Dermoscopy of a skin lesion: 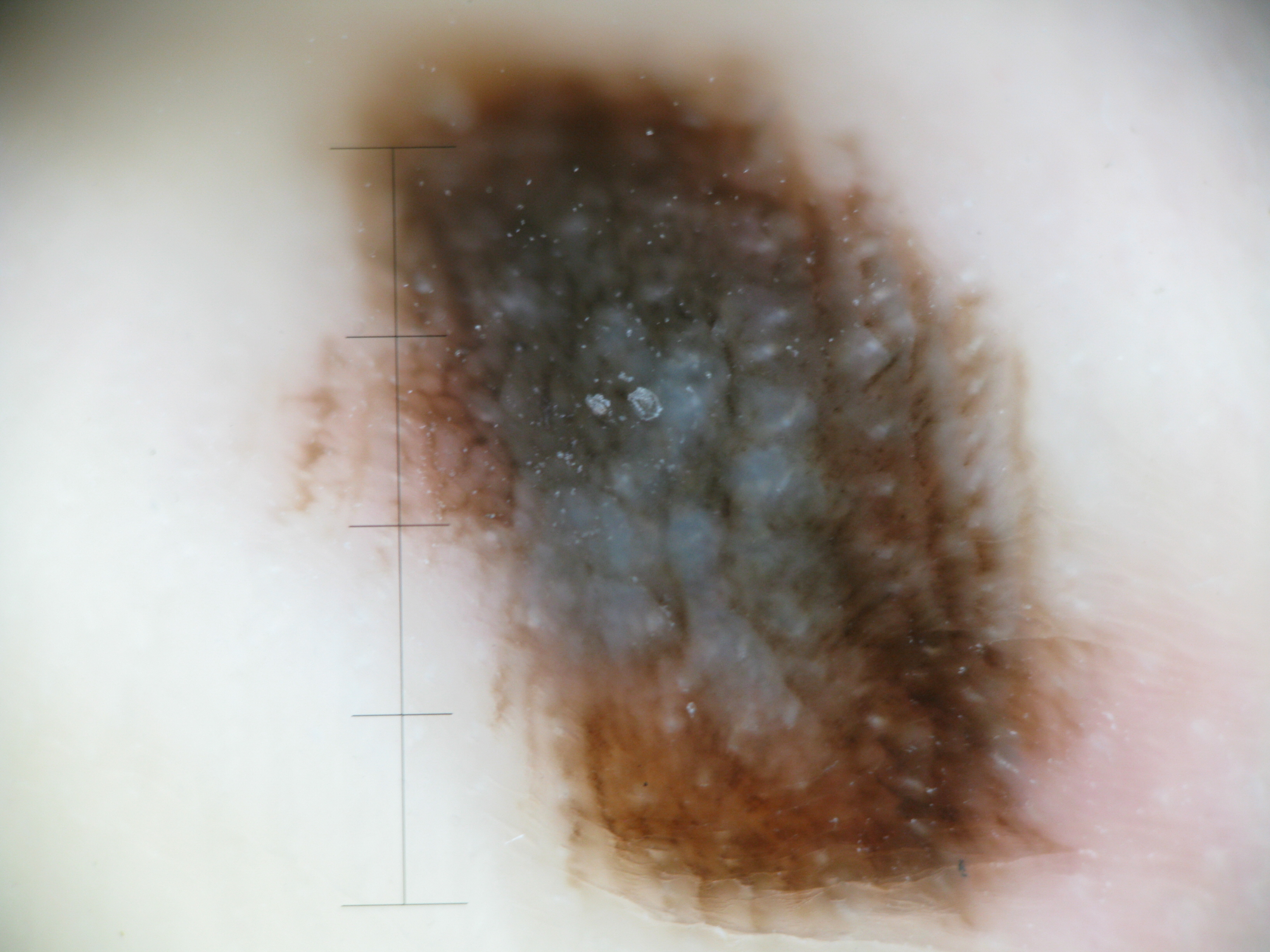  diagnosis:
    name: acral lentiginous melanoma
    code: alm
    malignancy: malignant
    super_class: melanocytic
    confirmation: histopathology